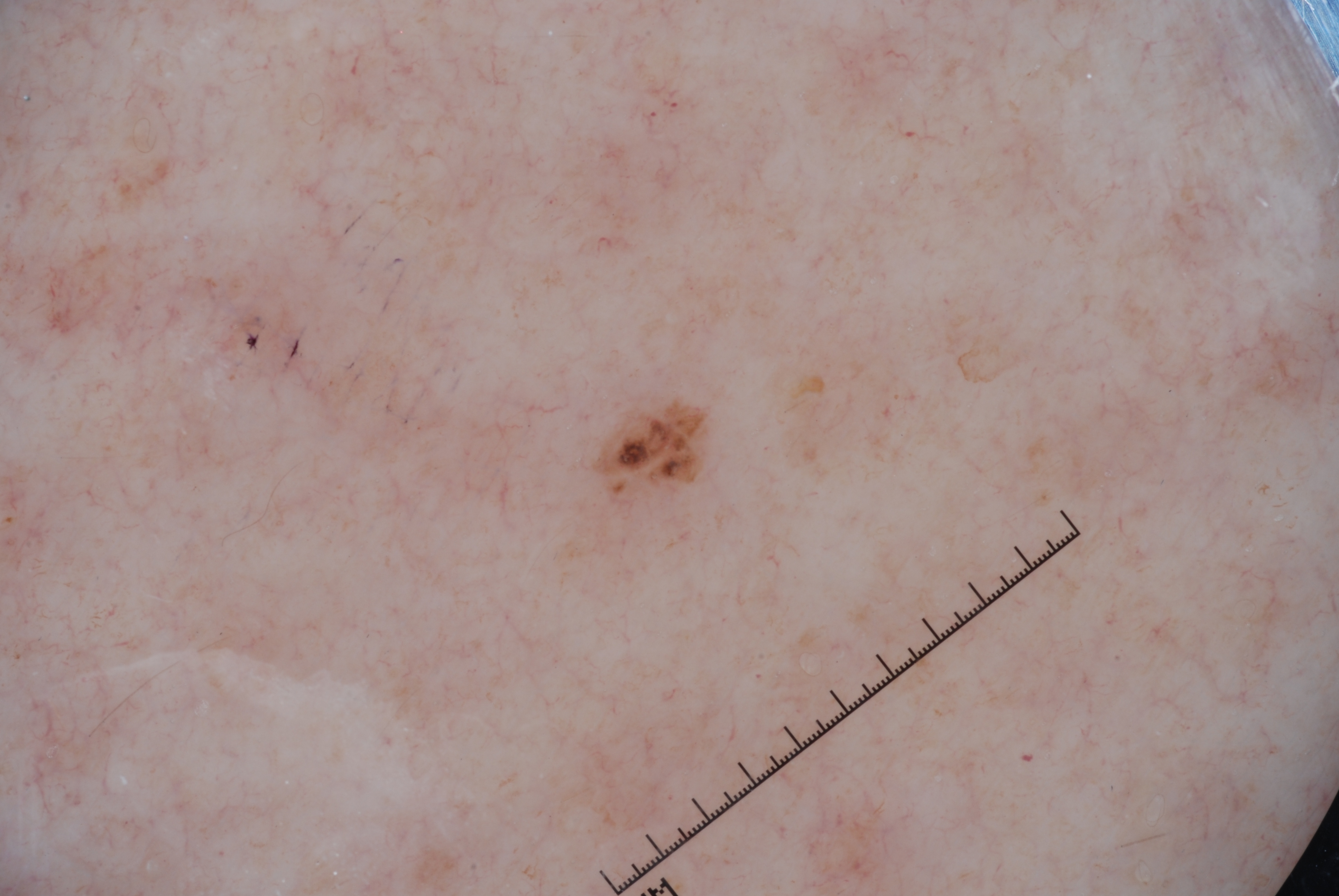Case summary:
A female subject, aged 43 to 47. A dermoscopic close-up of a skin lesion. The lesion is located at bbox=[597, 413, 701, 490]. Dermoscopic examination shows no milia-like cysts, negative network, streaks, or pigment network. A small lesion occupying a minor part of the field.
Conclusion:
Clinically diagnosed as a melanocytic nevus.